A clinical close-up photograph of a skin lesion · a male subject age 70 · by history, alcohol use and pesticide exposure — 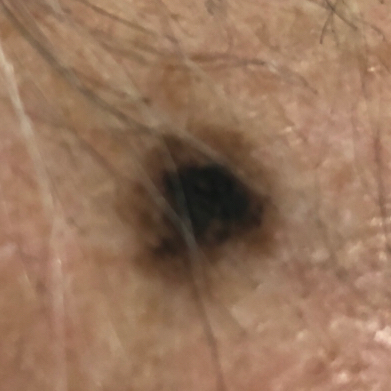Located on the face. The lesion is roughly 9 by 9 mm. The patient describes that the lesion has grown and has changed. Histopathology confirmed a melanoma.